A smartphone photograph of a skin lesion; a patient age 32:
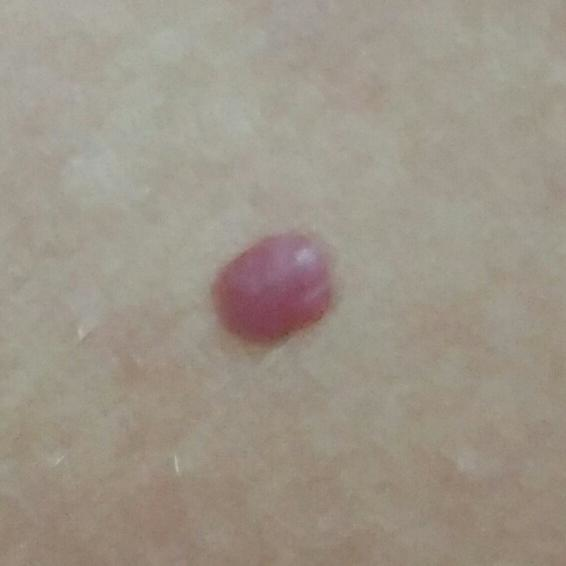Patient and lesion:
The lesion is on the back. The patient reports that the lesion has grown, itches, has bled, and is elevated, but does not hurt and has not changed.
Impression:
The consensus clinical diagnosis was a nevus.